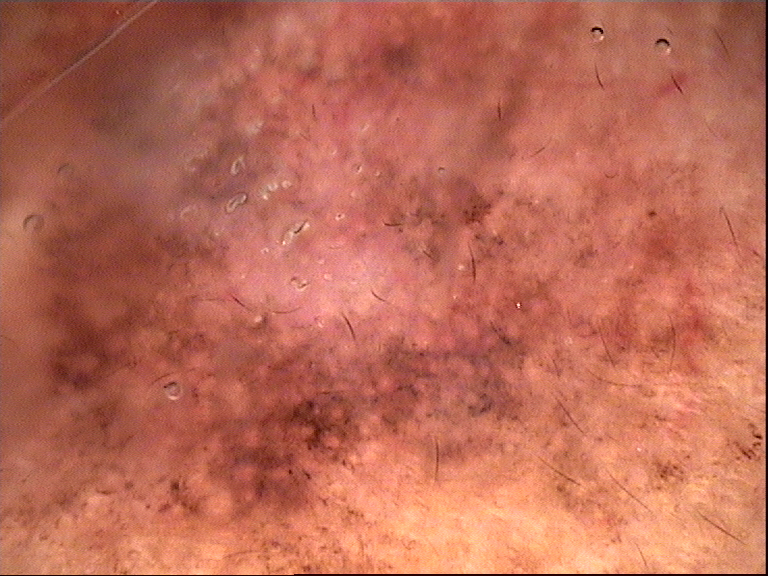Histopathologically confirmed as a lentigo maligna.